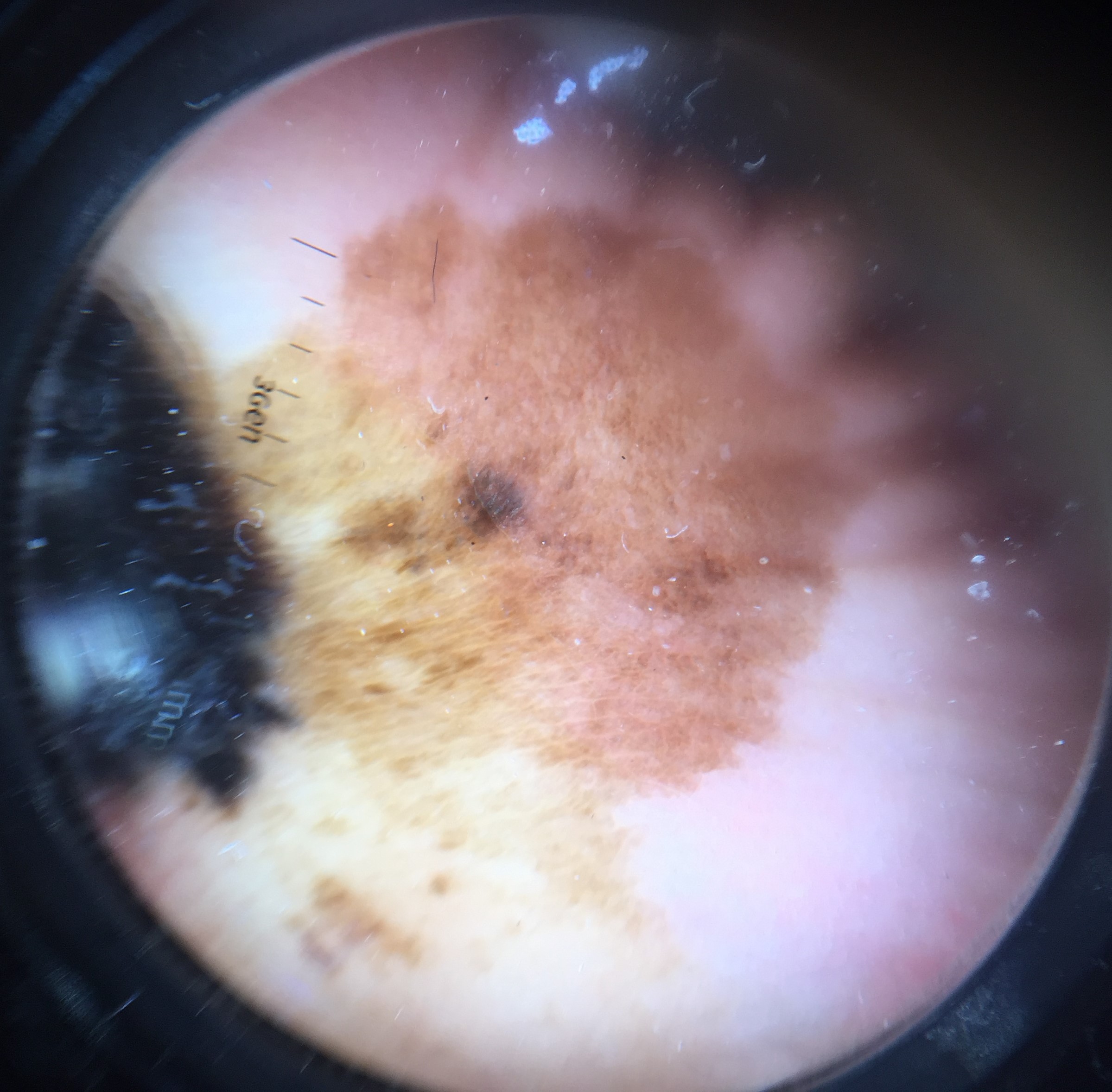Case:
– modality · dermatoscopy
– diagnosis · acral lentiginous melanoma (biopsy-proven)